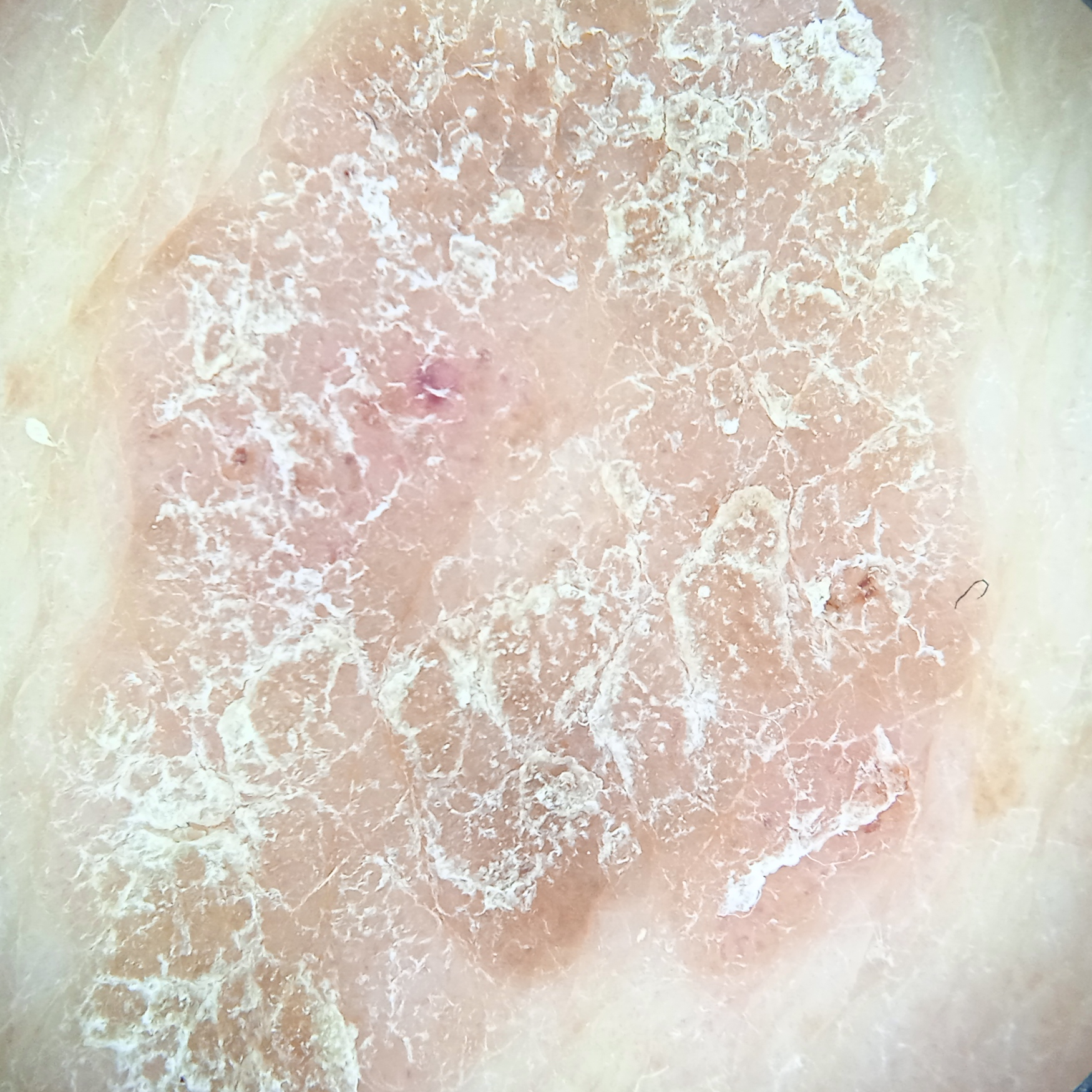The patient describes having few moles overall. The patient says their skin reddens with sun exposure. Imaged for a research study, with no referral diagnosis recorded. A dermoscopic image of a skin lesion. A male patient 72 years old. The patient reports a personal history of cancer, no personal history of skin cancer, and no immunosuppression. The lesion is about 16.5 mm across. The diagnostic impression was a seborrheic keratosis.